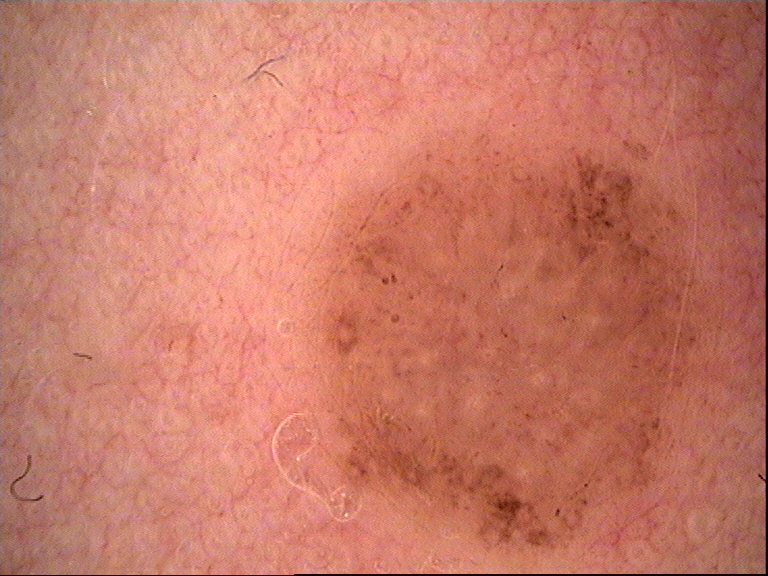image type=dermoscopy
subtype=banal
diagnosis=compound nevus (expert consensus)